A dermoscopic photograph of a skin lesion:
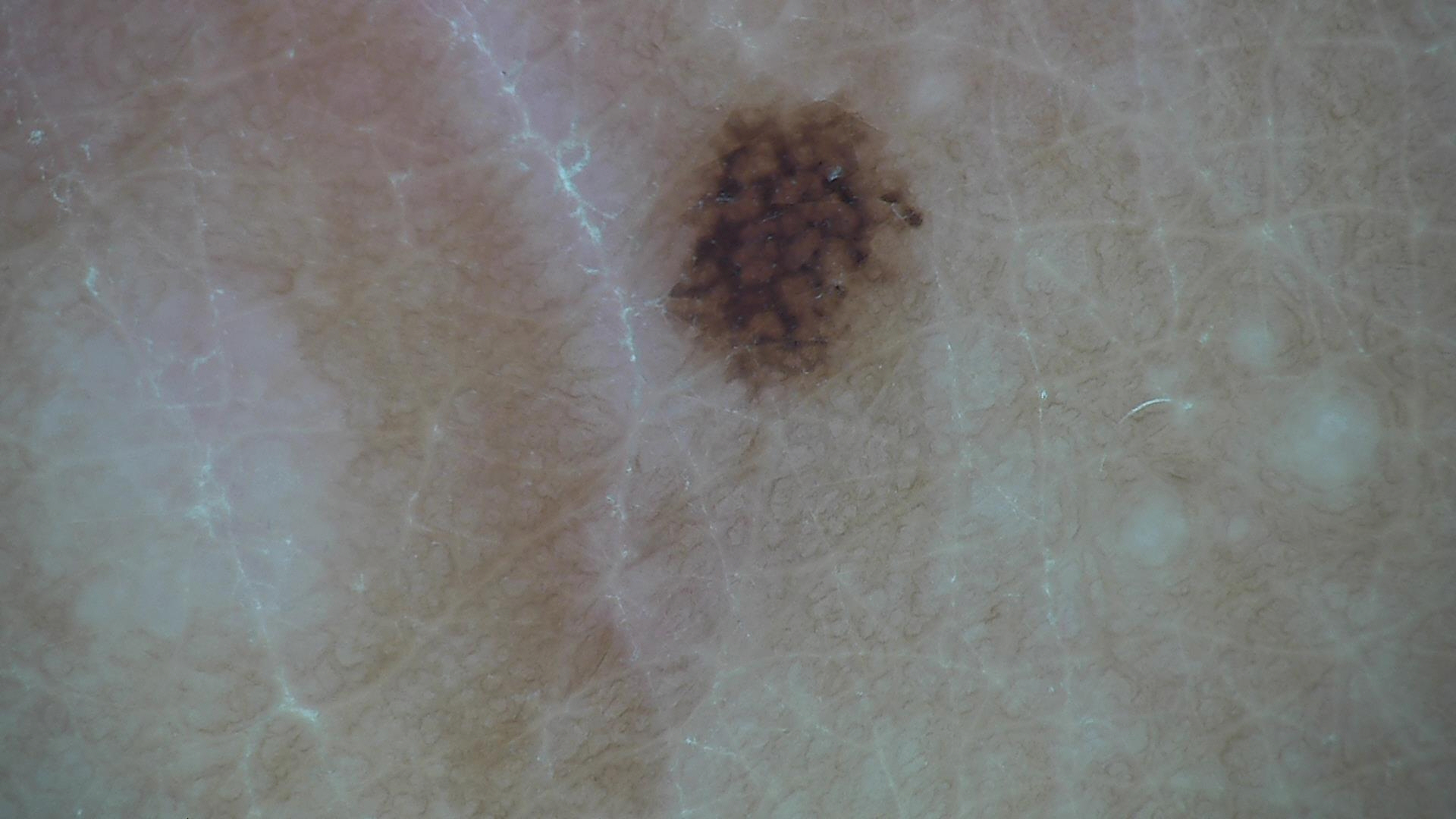Diagnosed as an acral dysplastic junctional nevus.